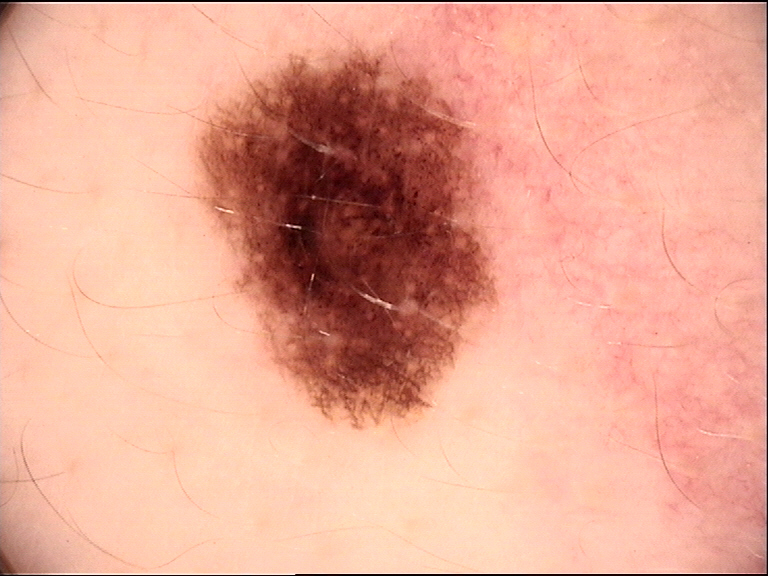Q: What is the imaging modality?
A: dermatoscopy
Q: What was the diagnostic impression?
A: dysplastic junctional nevus (expert consensus)